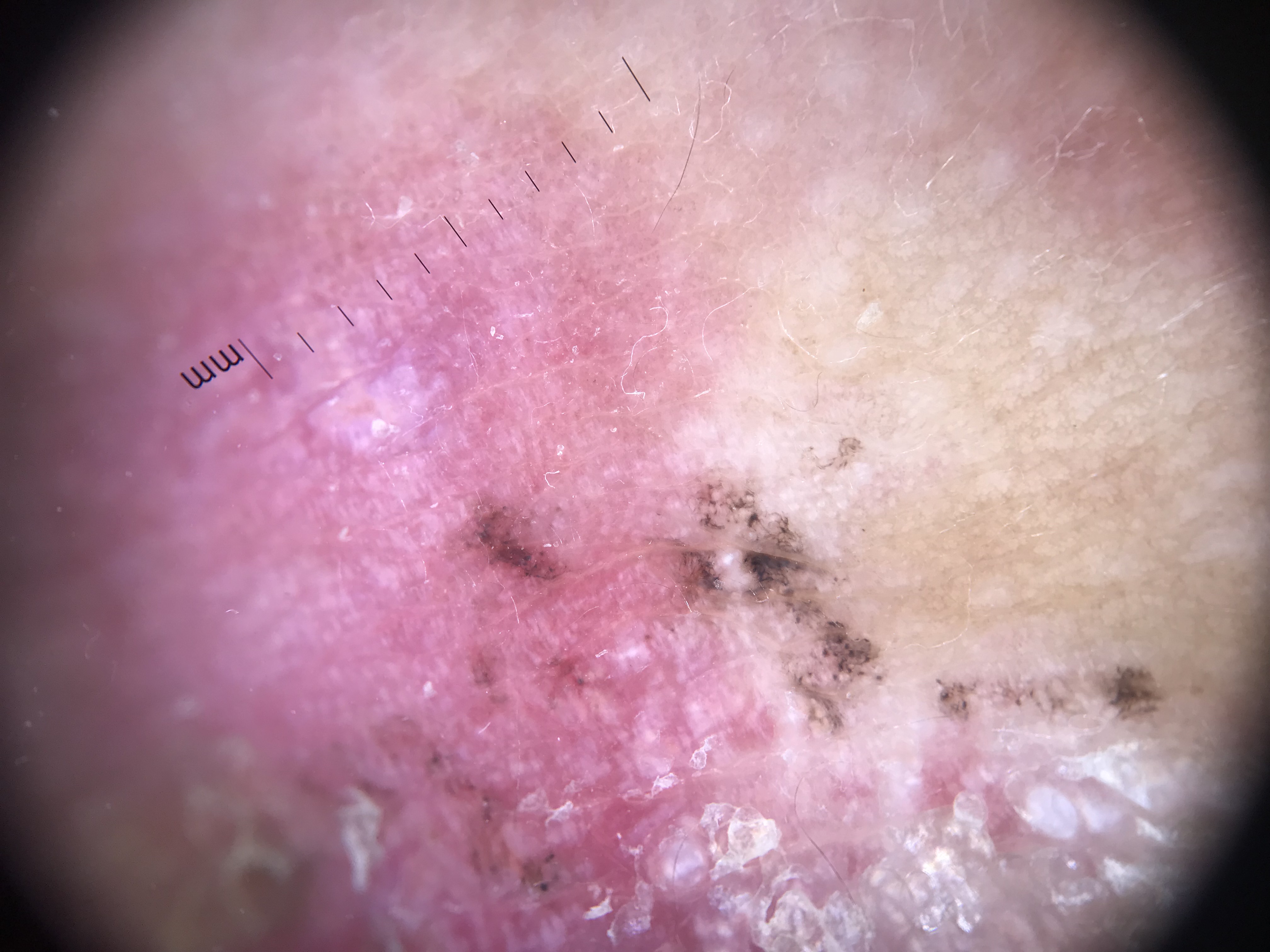| field | value |
|---|---|
| image type | dermoscopy |
| label | melanoma (biopsy-proven) |